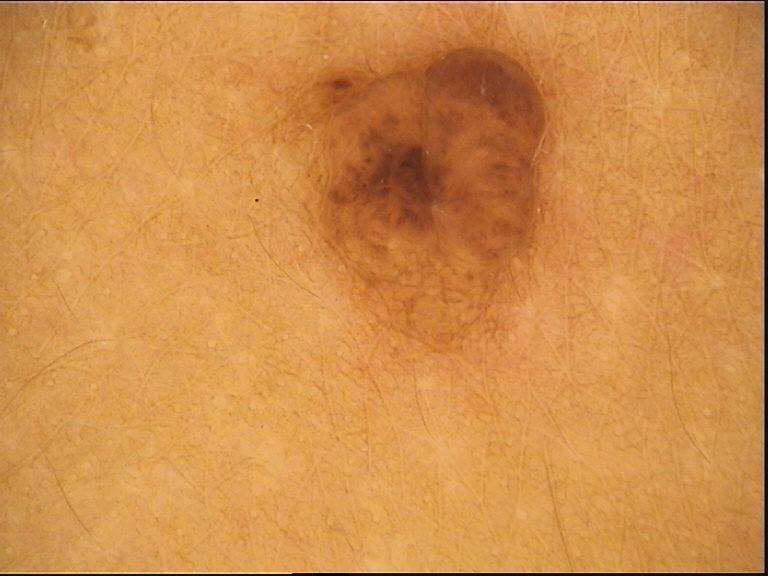The diagnostic label was a dermal nevus.